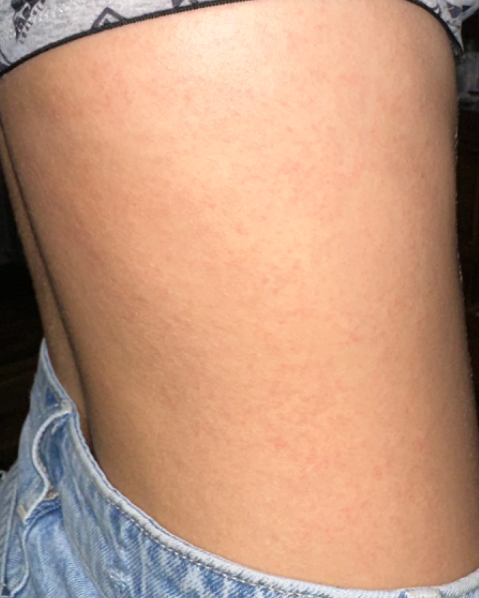The reviewer was unable to grade this case for skin condition. Reported lesion symptoms include itching and bothersome appearance. The back of the torso and leg are involved. The patient reports the condition has been present for about one day. The photo was captured at a distance. The subject is a female aged 18–29. The patient reports the lesion is flat.